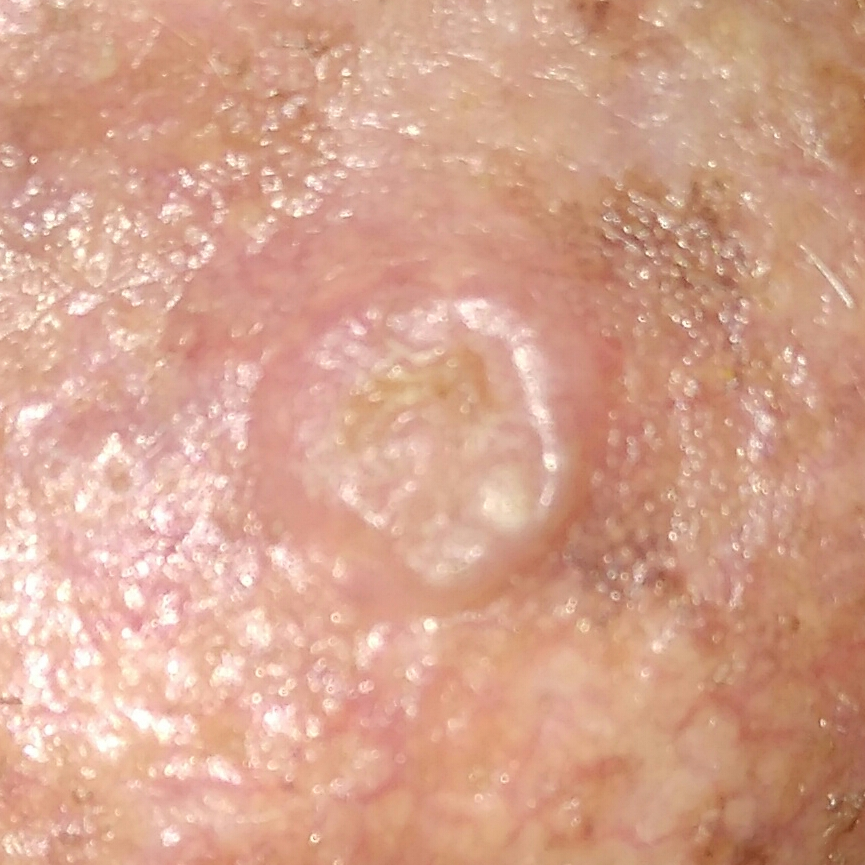Q: What is this lesion?
A: squamous cell carcinoma (biopsy-proven)